The lesion is associated with itching, skin tone: FST IV; lay graders estimated Monk skin tone scale 5–6, present for about one day, the patient is male, the affected area is the arm, an image taken at a distance, the patient considered this a rash — 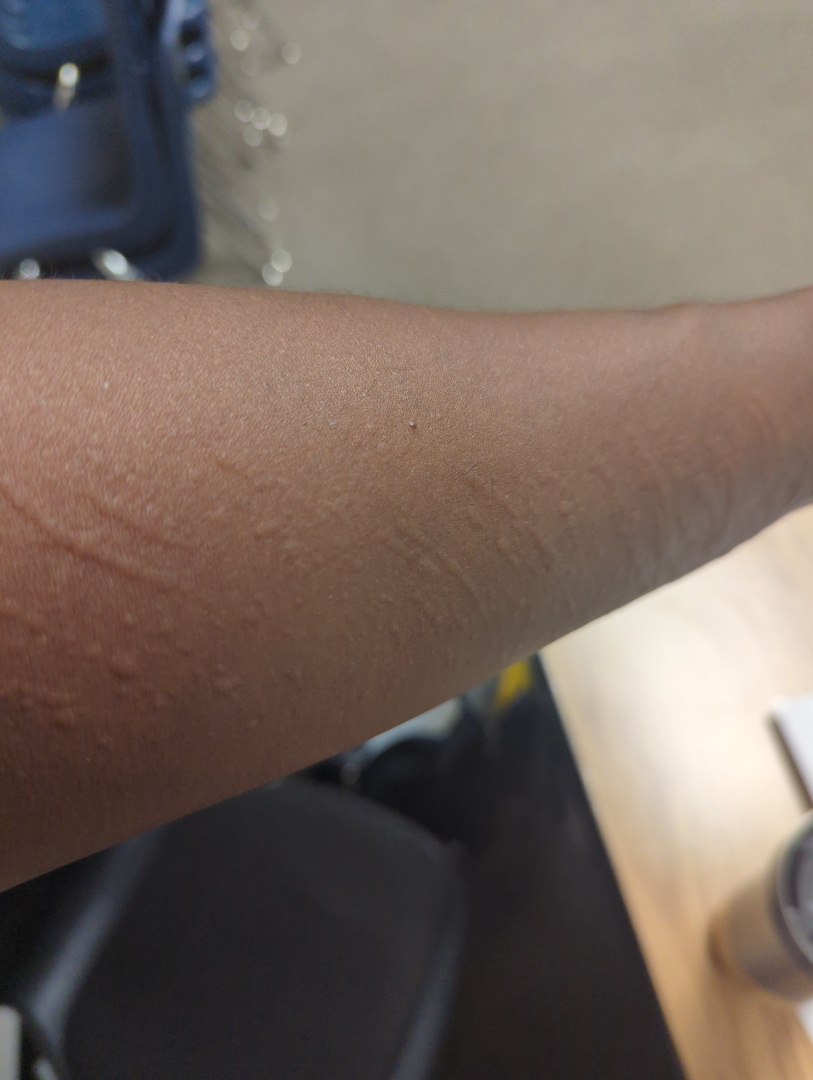diagnostic considerations = three independent reviewers: most likely Urticaria; less likely is Flagellate erythema; lower on the differential is Leukocytoclastic Vasculitis